A dermoscopic image of a skin lesion.
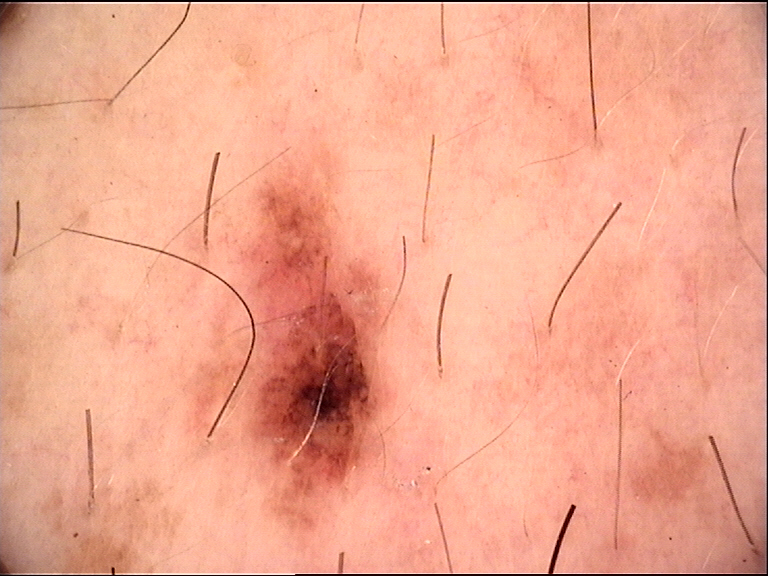Impression: The diagnosis was a dysplastic compound nevus.